The affected area is the leg; texture is reported as raised or bumpy; the patient described the issue as a rash; reported duration is one to four weeks; a close-up photograph:
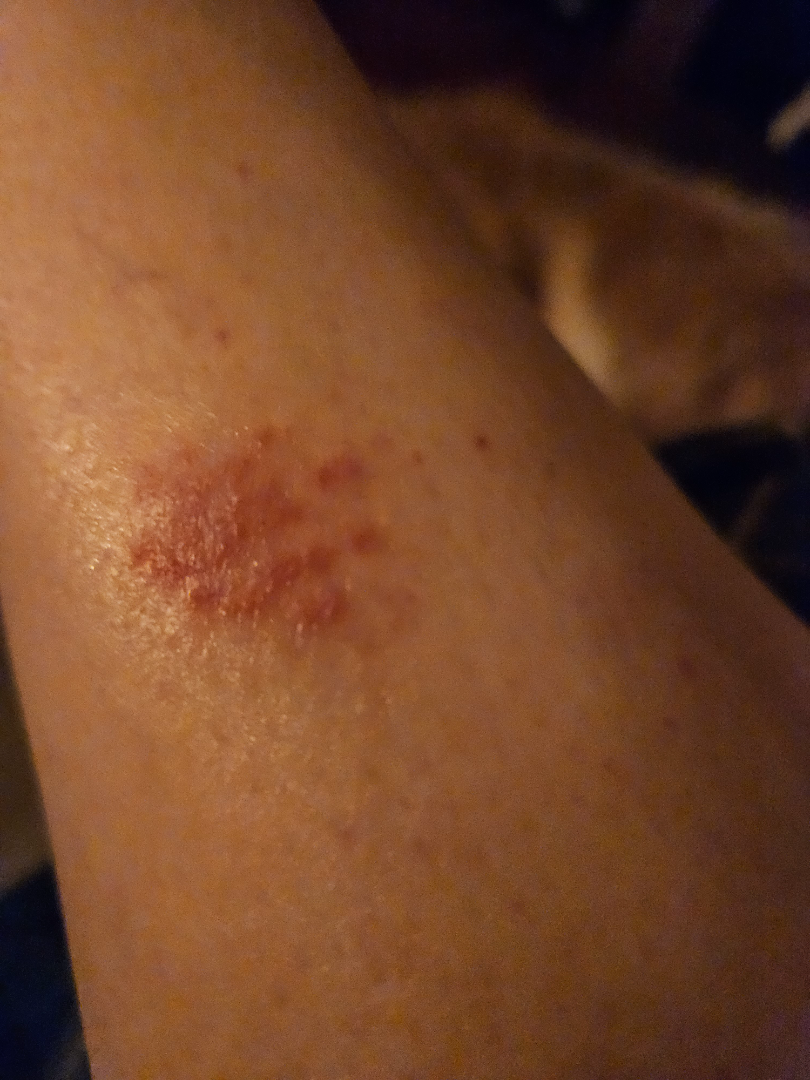• dermatologist impression: in keeping with Eczema